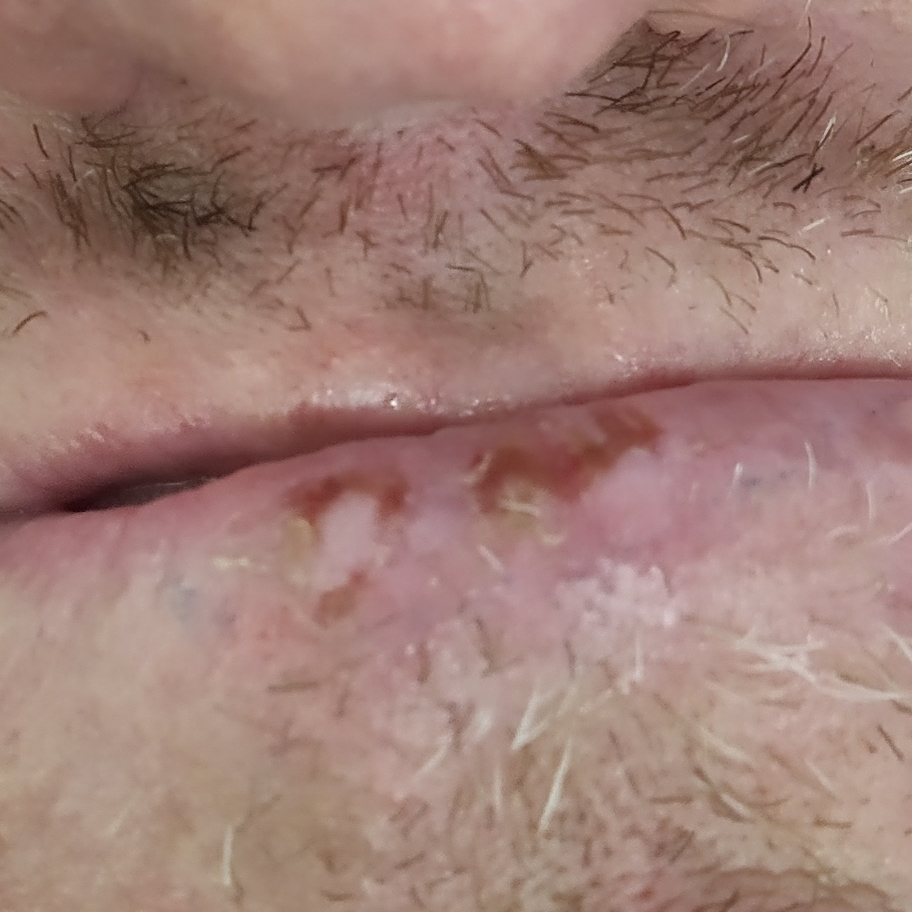Case:
* diagnostic label · squamous cell carcinoma (biopsy-proven)